A dermoscopy image of a single skin lesion:
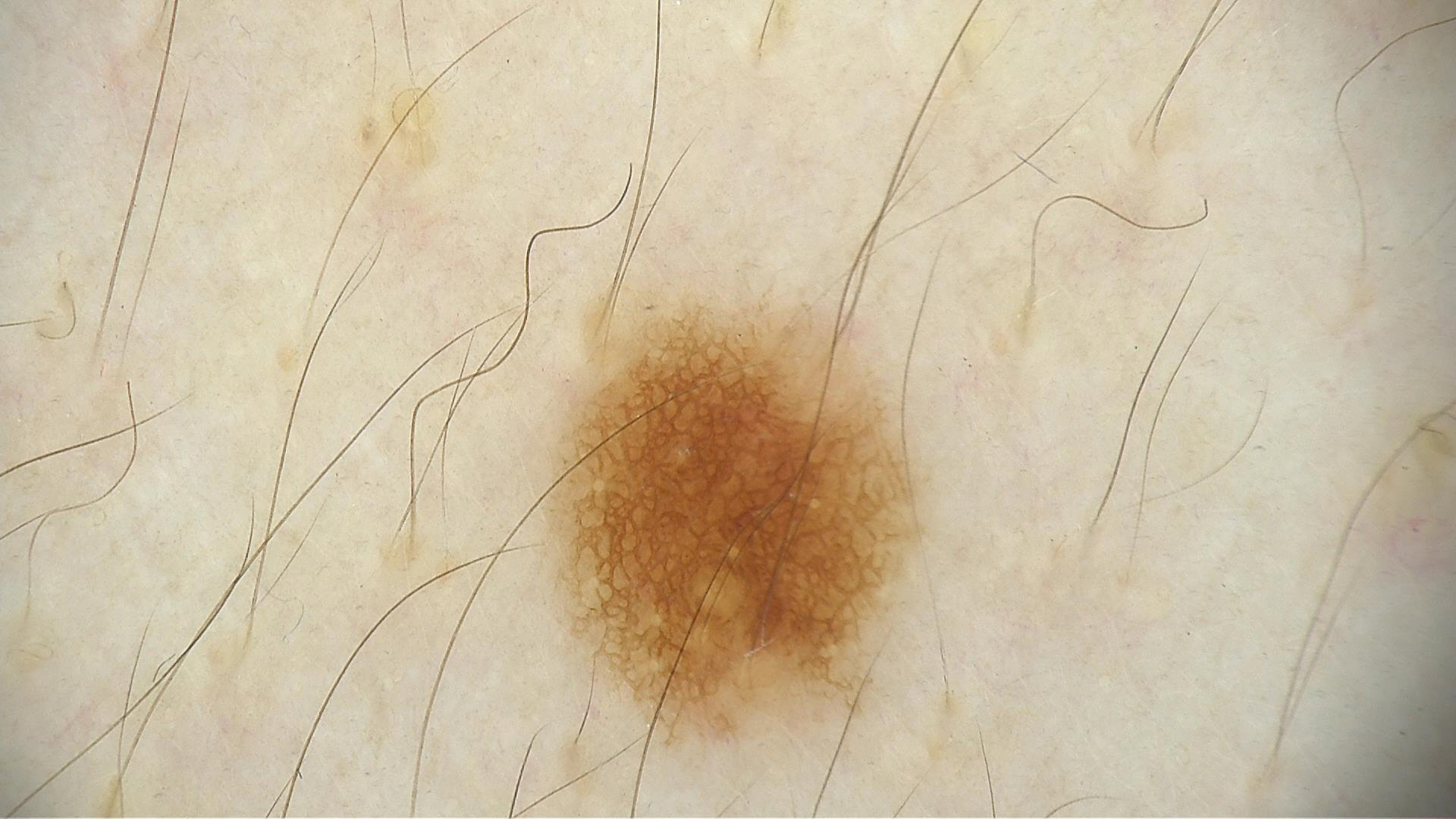<lesion>
<diagnosis>
<name>dysplastic junctional nevus</name>
<code>jd</code>
<malignancy>benign</malignancy>
<super_class>melanocytic</super_class>
<confirmation>expert consensus</confirmation>
</diagnosis>
</lesion>